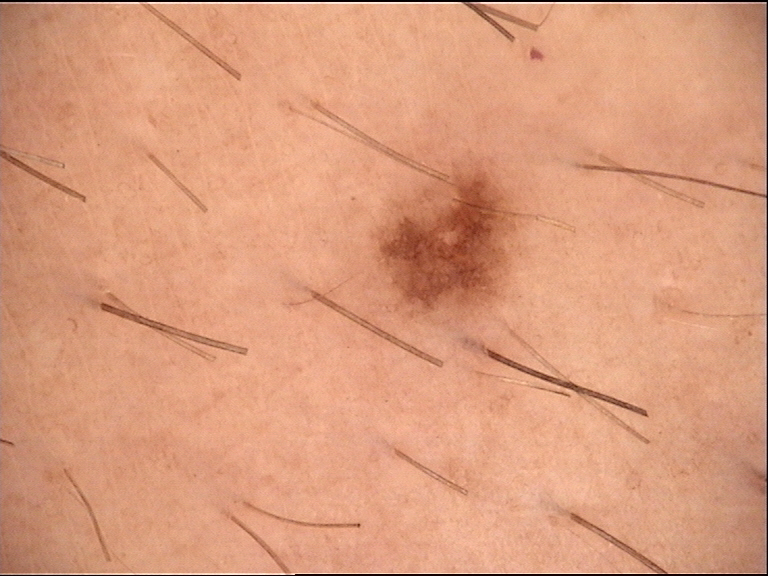Findings:
A dermoscopic close-up of a skin lesion.
Conclusion:
Classified as a dysplastic junctional nevus.